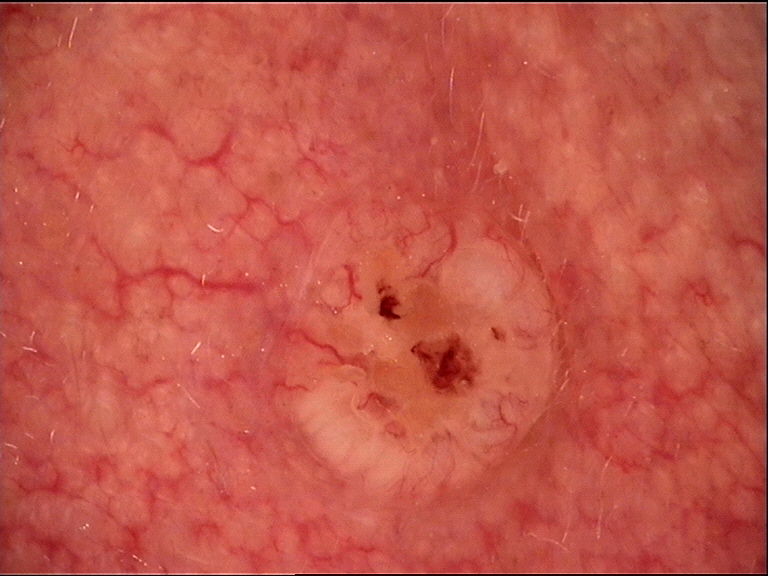A dermoscopic photograph of a skin lesion.
The architecture is that of a keratinocytic lesion.
Biopsy-confirmed as a malignant lesion — a basal cell carcinoma.